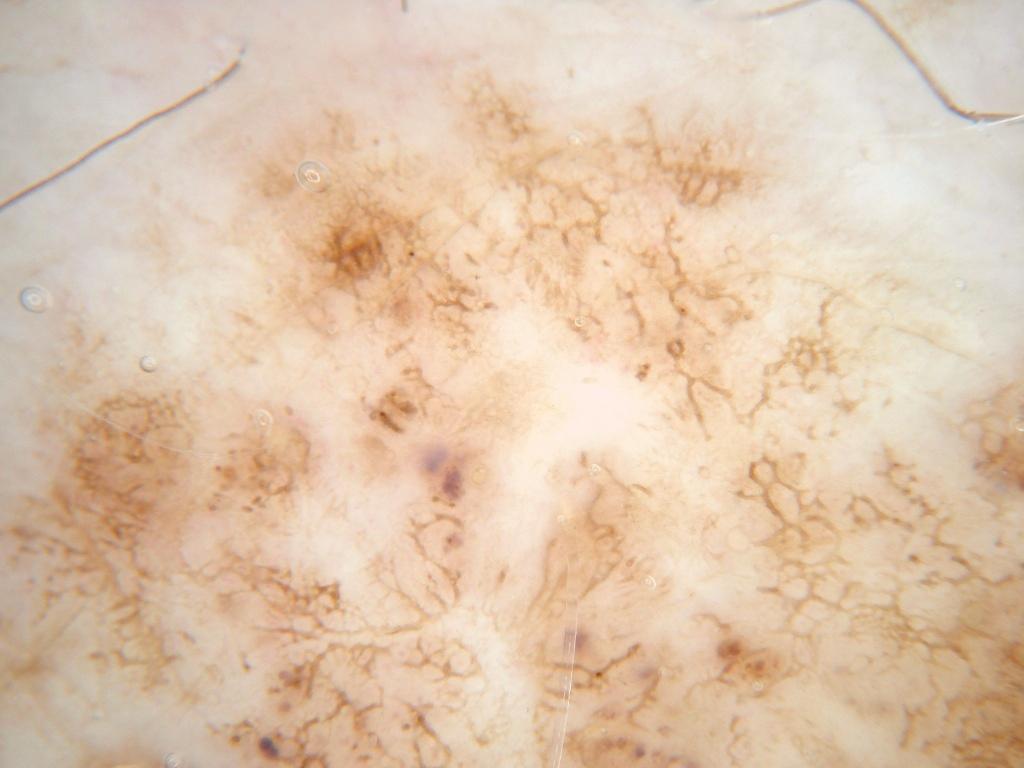Image and clinical context: A male subject aged approximately 80. A dermoscopic image of a skin lesion. The lesion extends across almost the whole field of view. Dermoscopic assessment notes pigment network. Impression: Expert review diagnosed this as a melanocytic nevus.